Symptoms reported: bothersome appearance. The affected area is the leg. Female subject, age 30–39. Close-up view. Fitzpatrick skin type II; human graders estimated Monk Skin Tone 1 or 2 (two reviewer pools). The patient described the issue as a rash. The patient notes the condition has been present for about one day. The patient notes the lesion is flat: 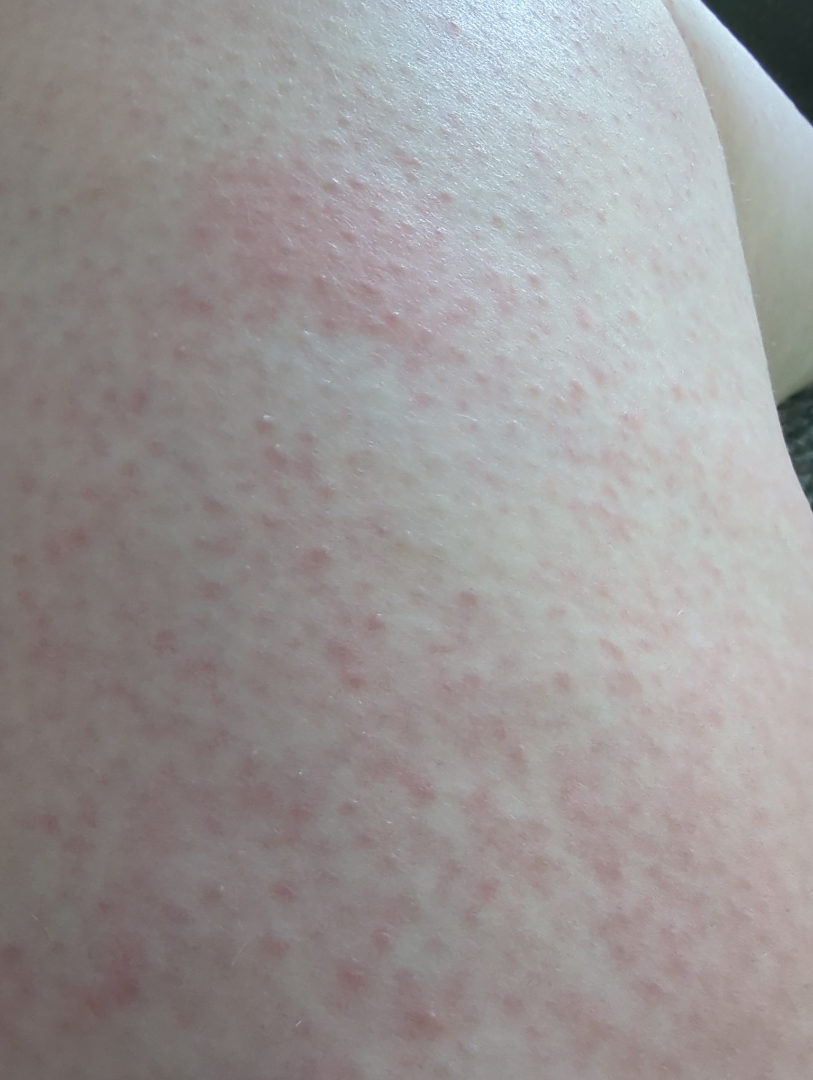Q: What is the differential diagnosis?
A: reviewed remotely by three dermatologists: Eczema and Drug Rash were each considered, in no particular order; a more distant consideration is Viral Exanthem; less likely is Hypersensitivity